A dermoscopy image of a single skin lesion.
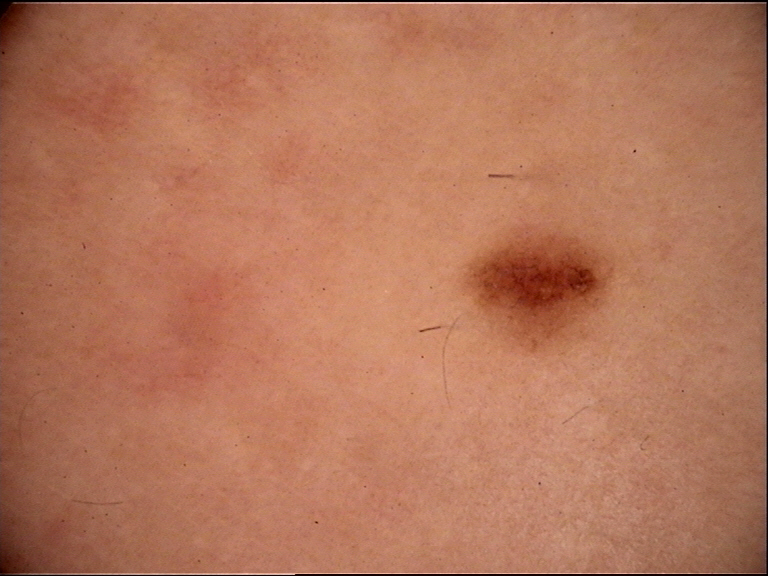Labeled as a benign lesion — a dysplastic junctional nevus.